The photograph was taken at a distance; the affected area is the back of the torso, back of the hand, head or neck and arm.
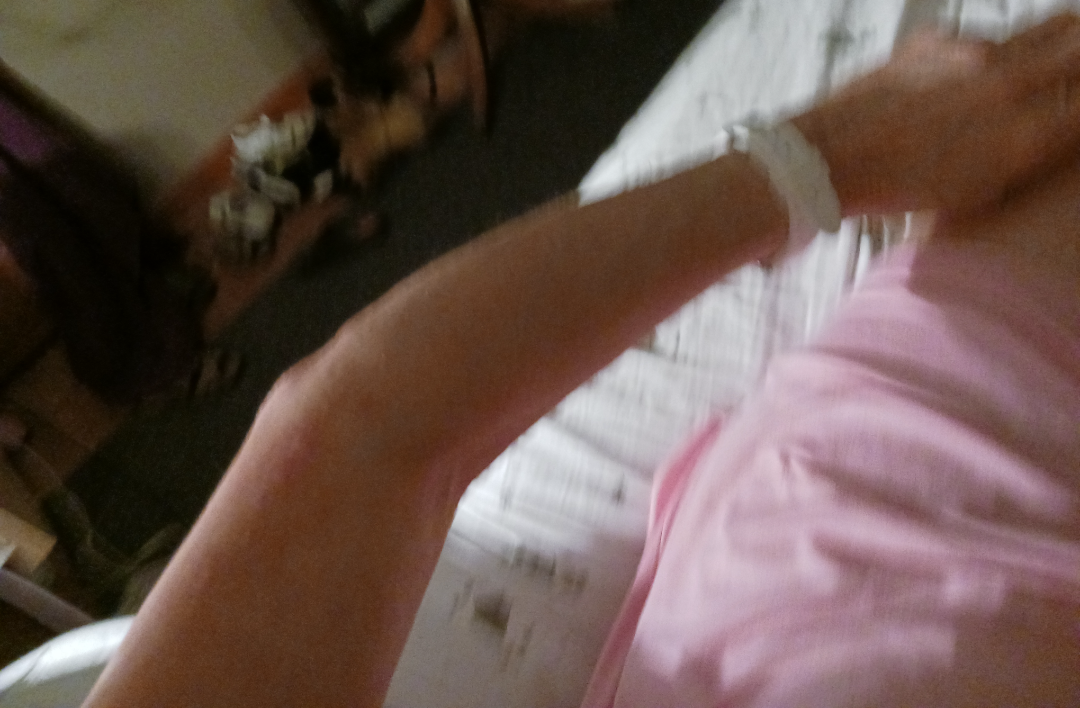The skin condition could not be confidently assessed from this image. Lay reviewers estimated MST 2 or 4. Present for one to four weeks. Reported lesion symptoms include itching, darkening, pain, burning and bothersome appearance. Associated systemic symptoms include mouth sores. The patient described the issue as a nail problem.